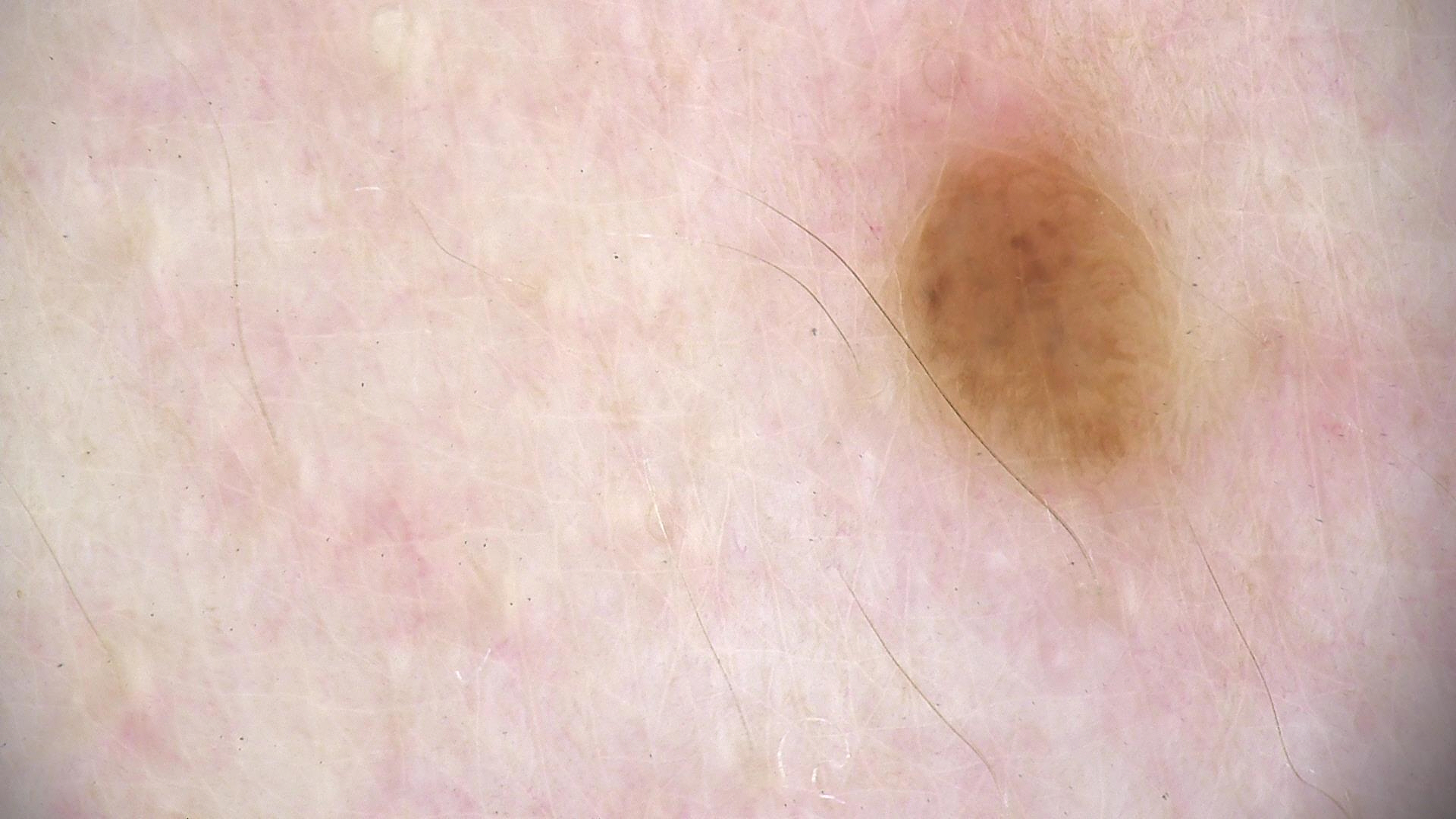Diagnosed as a banal lesion — a dermal nevus.